This image was taken at an angle · the lesion involves the arm:
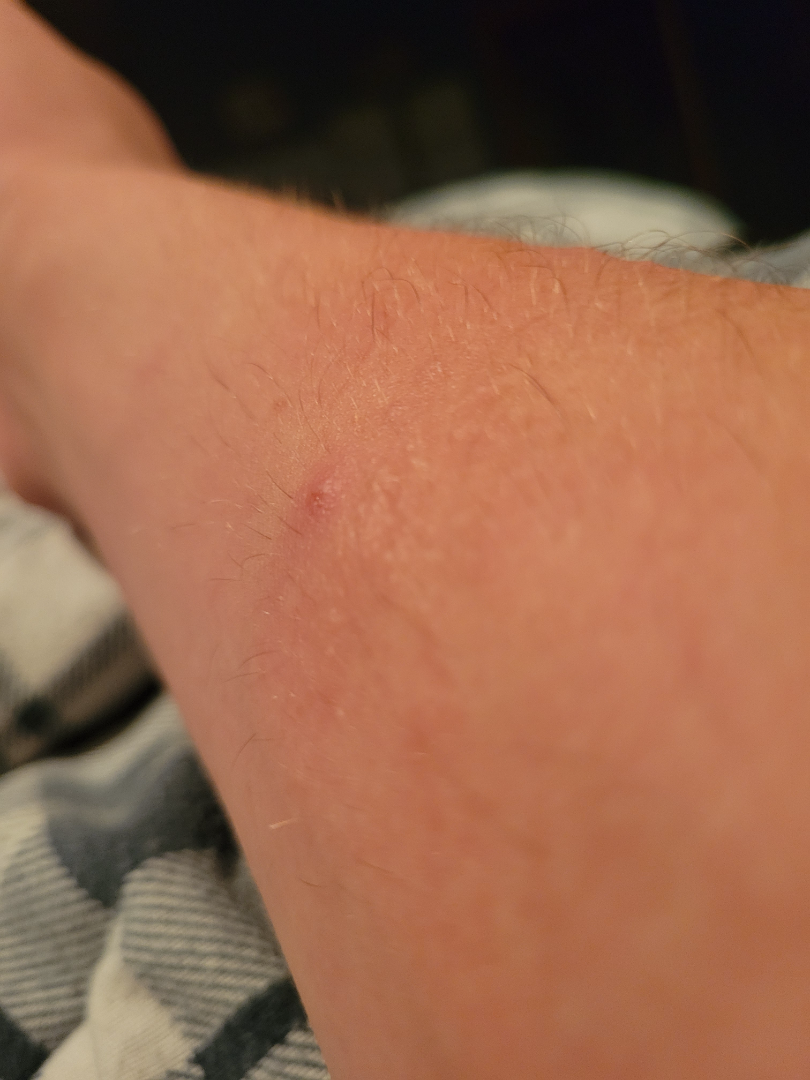assessment: could not be assessed | skin tone: Fitzpatrick III | symptoms: itching | symptom duration: less than one week | described texture: raised or bumpy and fluid-filled | associated systemic symptoms: joint pain | self-categorized as: a rash.